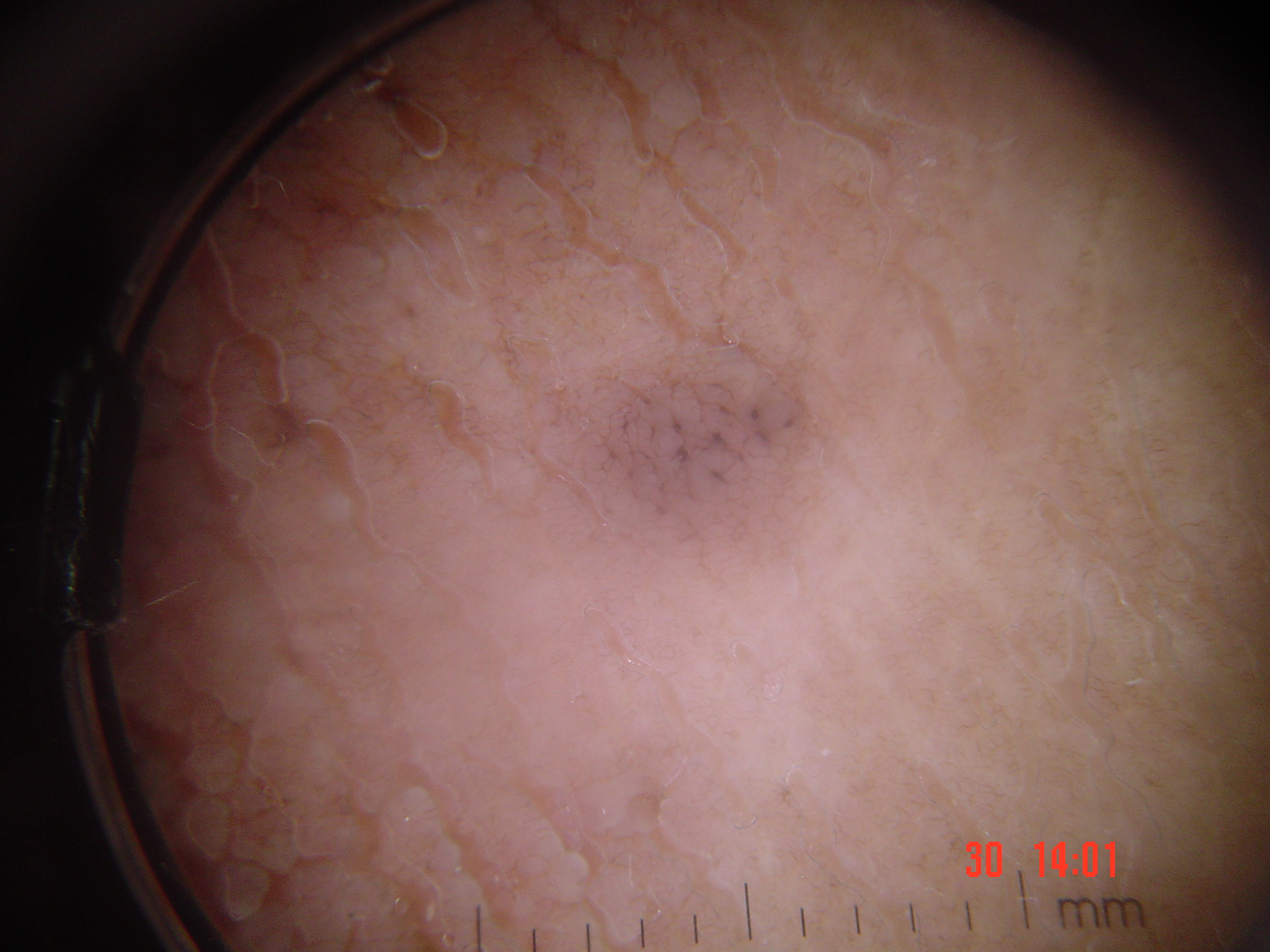{
  "image": "dermoscopy",
  "lesion_type": {
    "main_class": "keratinocytic"
  },
  "diagnosis": {
    "name": "seborrheic keratosis",
    "code": "sk",
    "malignancy": "benign",
    "super_class": "non-melanocytic",
    "confirmation": "expert consensus"
  }
}